A skin lesion imaged with a dermatoscope.
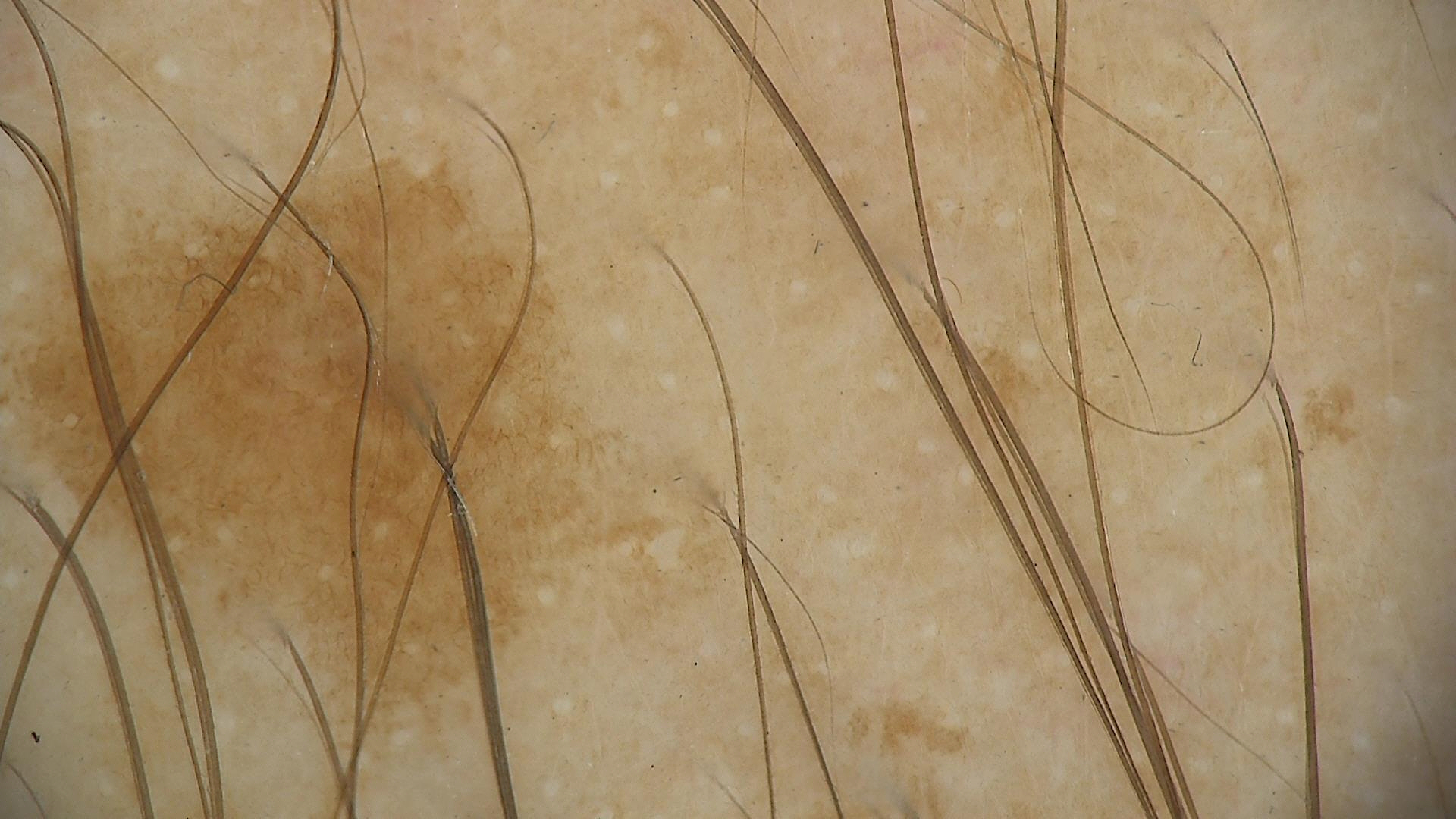  diagnosis:
    name: solar lentigo
    code: sl
    malignancy: benign
    super_class: melanocytic
    confirmation: expert consensus